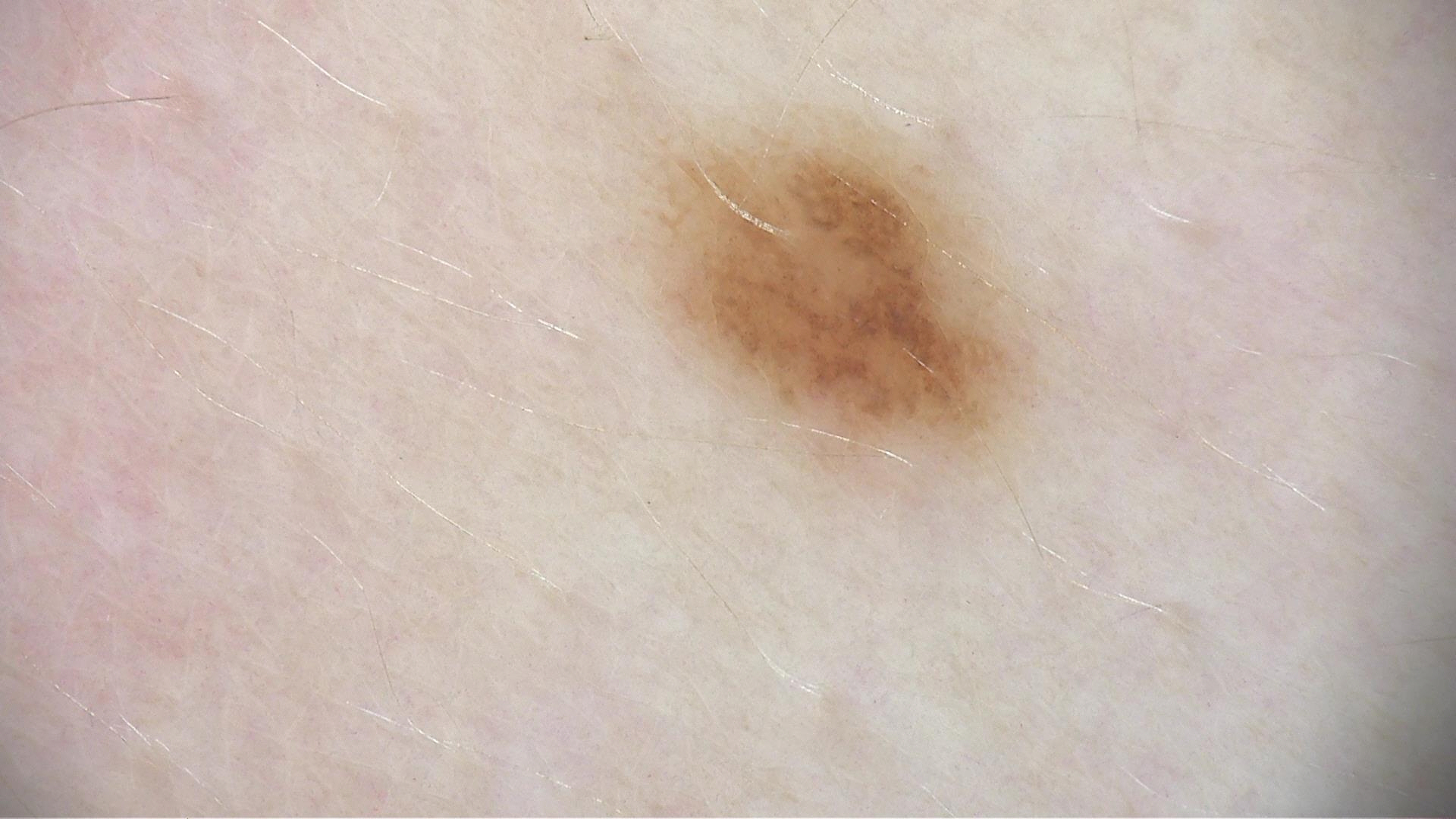modality = dermoscopy | class = dysplastic junctional nevus (expert consensus).